Dermoscopy of a skin lesion: 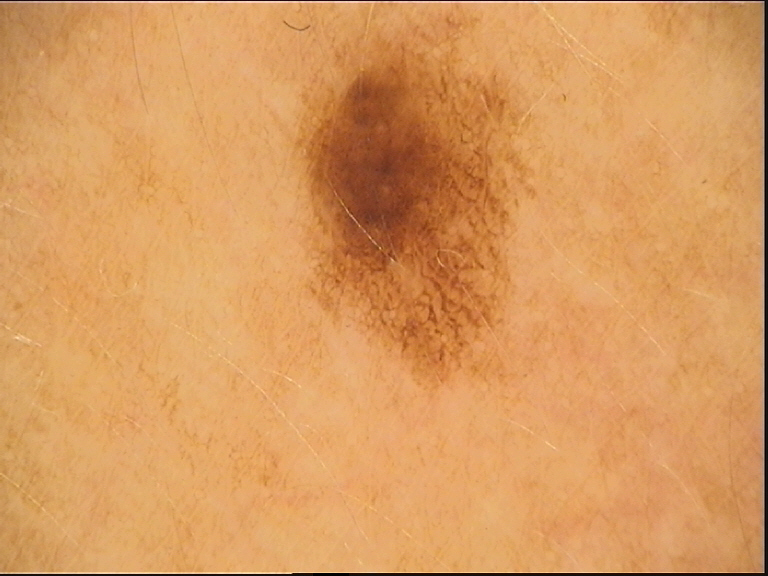{"diagnosis": {"name": "dysplastic junctional nevus", "code": "jd", "malignancy": "benign", "super_class": "melanocytic", "confirmation": "expert consensus"}}